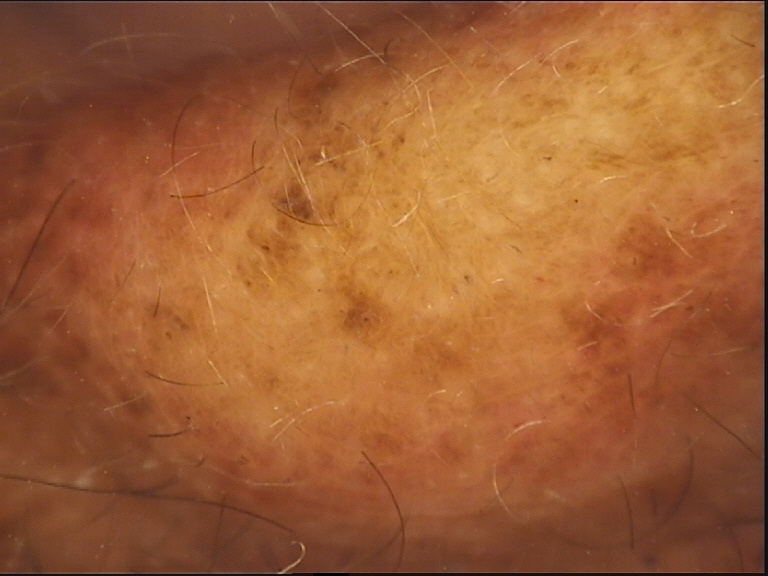{
  "diagnosis": {
    "name": "congenital compound nevus",
    "code": "ccb",
    "malignancy": "benign",
    "super_class": "melanocytic",
    "confirmation": "expert consensus"
  }
}